A female subject aged around 70 · dermoscopy of a skin lesion: 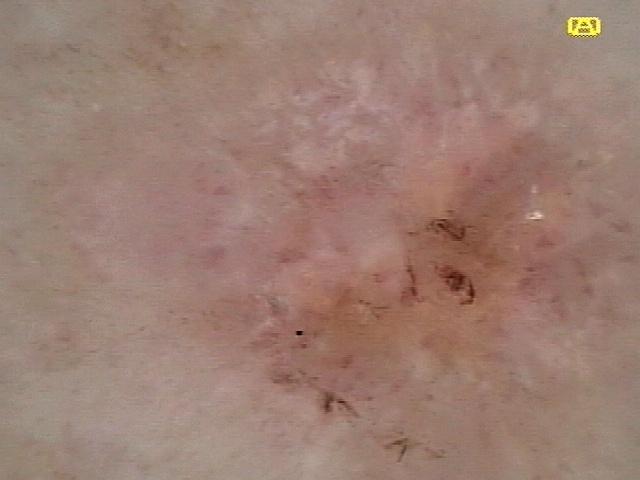{
  "lesion_location": {
    "region": "a lower extremity"
  },
  "diagnosis": {
    "name": "Basal cell carcinoma",
    "malignancy": "malignant",
    "confirmation": "histopathology",
    "lineage": "adnexal"
  }
}